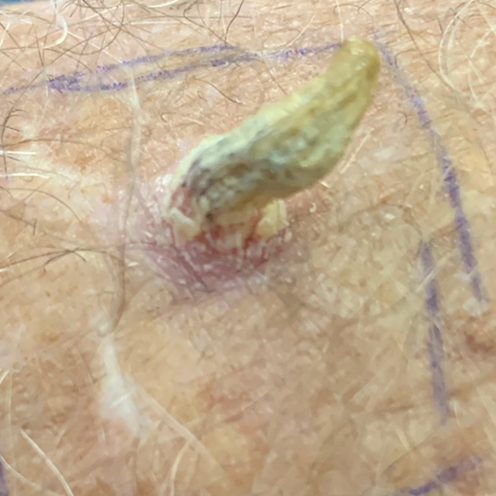A male patient aged 71. The patient is FST II. The chart notes alcohol use and no prior malignancy (patient or family). A clinical photograph showing a skin lesion. The lesion is located on a forearm. The lesion measures approximately 7 × 5 mm. The patient describes that the lesion has grown, is elevated, and hurts. Histopathologically confirmed as a lesion of indeterminate malignant potential — an actinic keratosis.